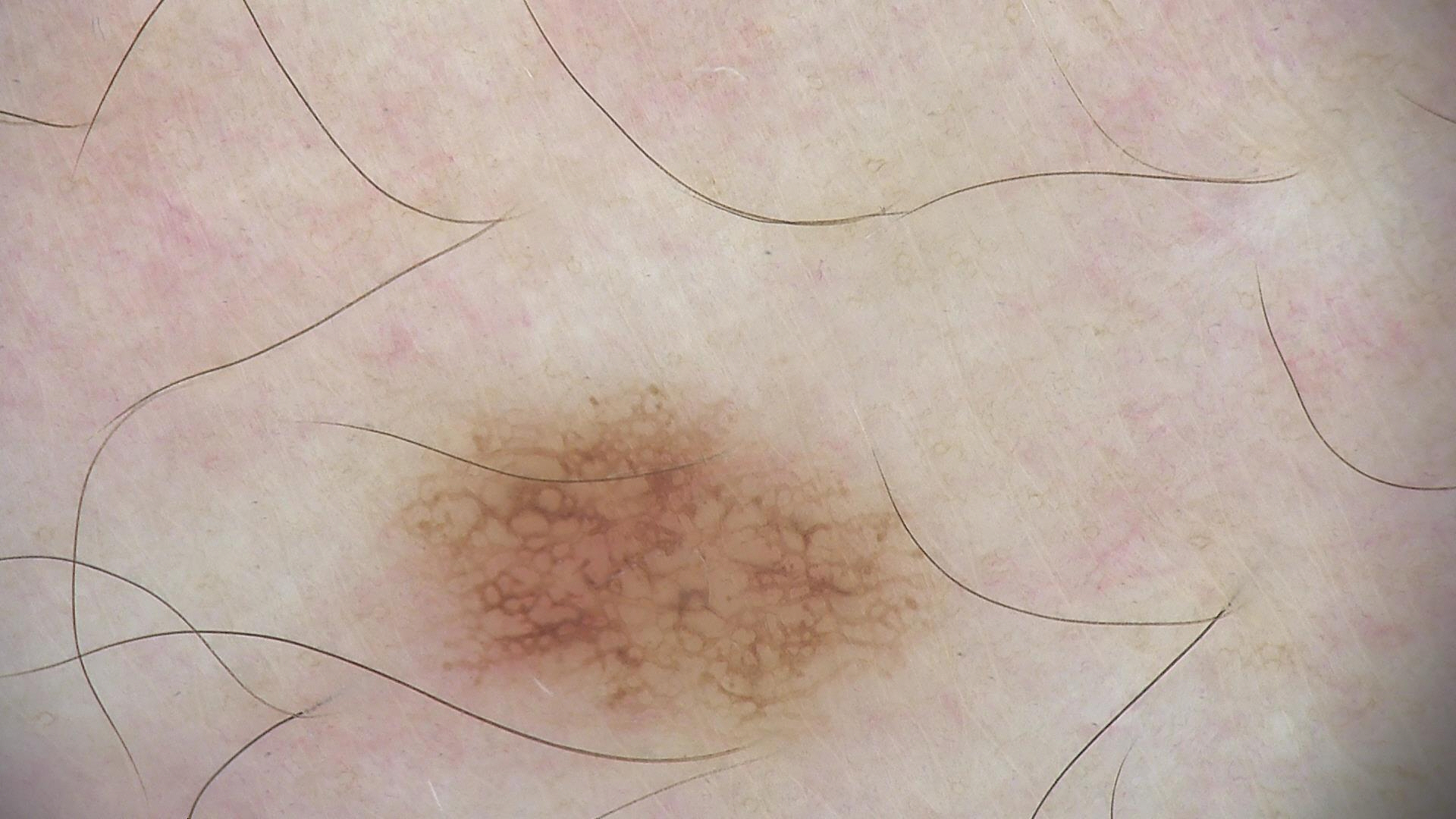A skin lesion imaged with a dermatoscope. The diagnosis was a dysplastic junctional nevus.